This image was taken at a distance. Located on the head or neck. Female patient, age 18–29: 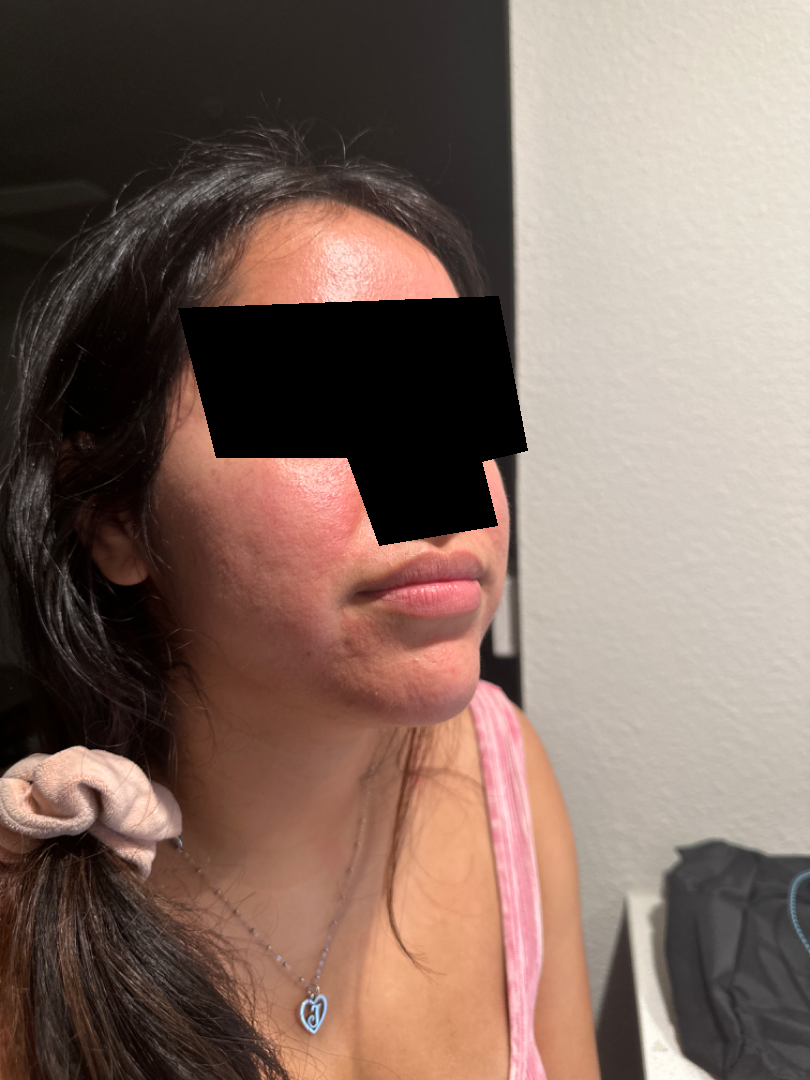{"patient_category": "a rash", "systemic_symptoms": "none reported", "duration": "about one day", "texture": "raised or bumpy", "symptoms": "itching", "differential": {"leading": ["Rosacea"]}}